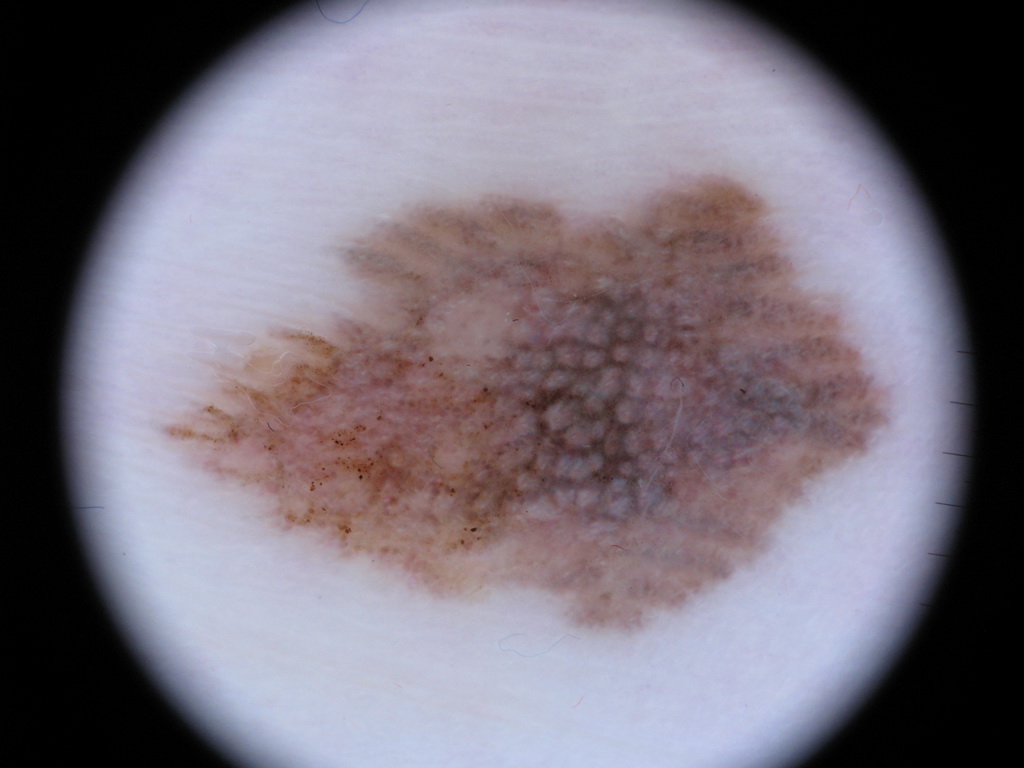A dermatoscopic image of a skin lesion.
In (x1, y1, x2, y2) order, the lesion is bounded by 164 165 890 632.
A moderately sized lesion.
Histopathological examination showed a skin cancer.